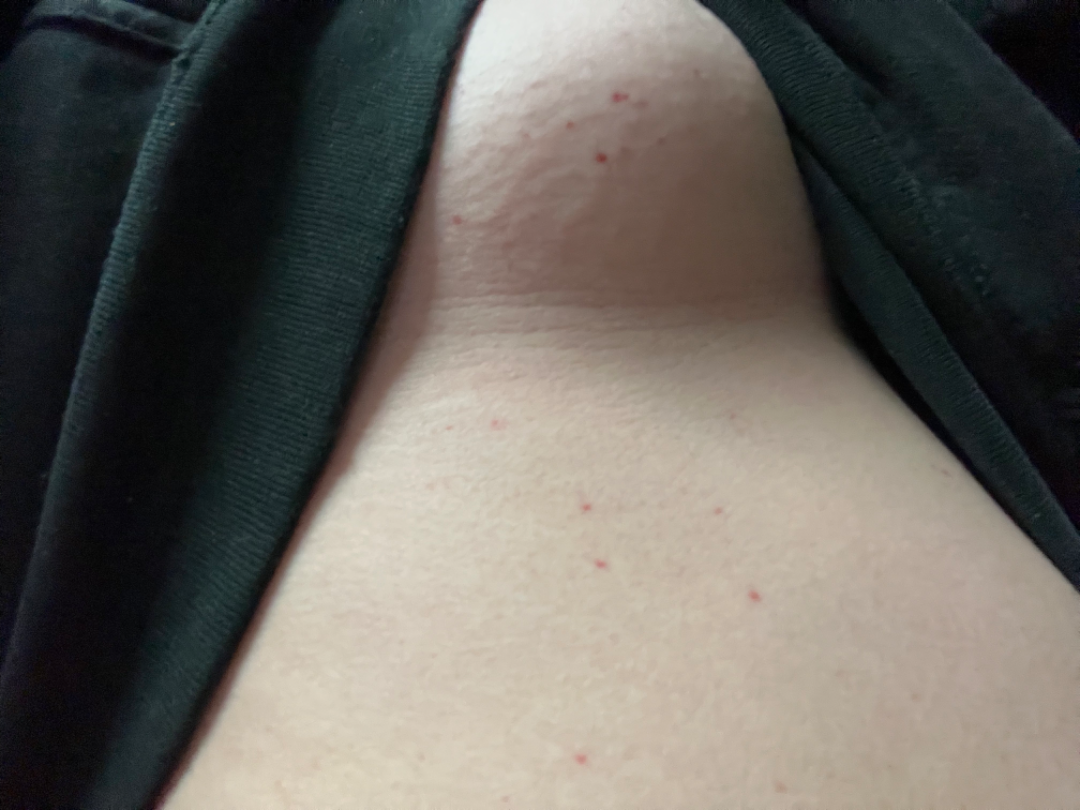The condition has been present for one to three months. Self-categorized by the patient as a rash. Reported lesion symptoms include itching and bothersome appearance. Associated systemic symptoms include fatigue and joint pain. The photograph is a close-up of the affected area. The affected area is the back of the torso, front of the torso and leg. Female subject, age 18–29. The reviewing dermatologist's impression was: consistent with Hemangioma.